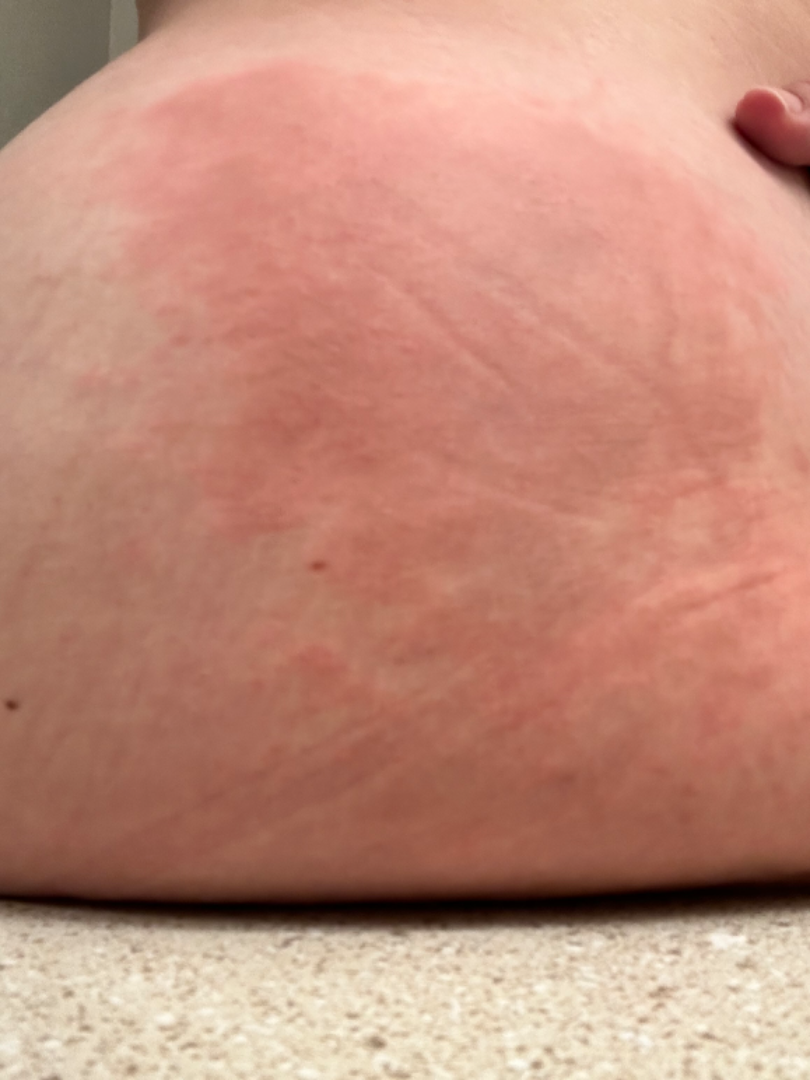The favored diagnosis is Allergic Contact Dermatitis; also on the differential is Cellulitis; possibly Erythema migrans.